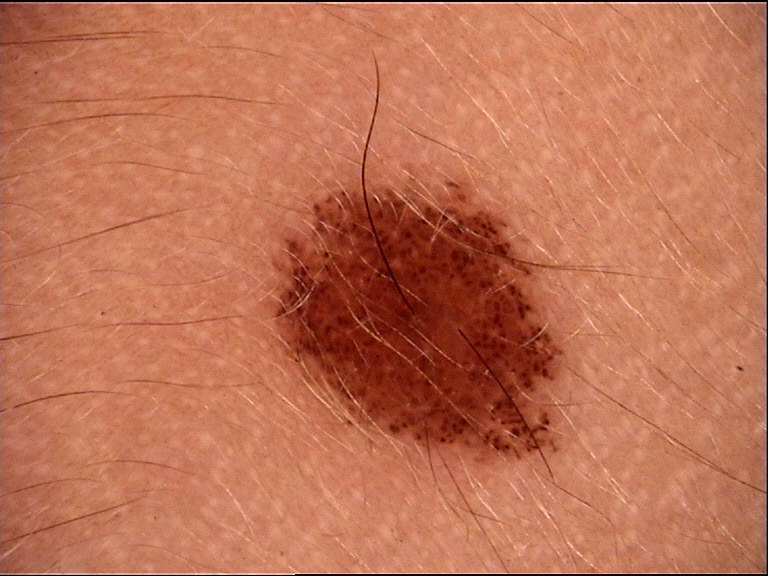  diagnosis:
    name: dysplastic junctional nevus
    code: jd
    malignancy: benign
    super_class: melanocytic
    confirmation: expert consensus